A female patient in their mid-80s or older, a dermoscopic close-up of a skin lesion:
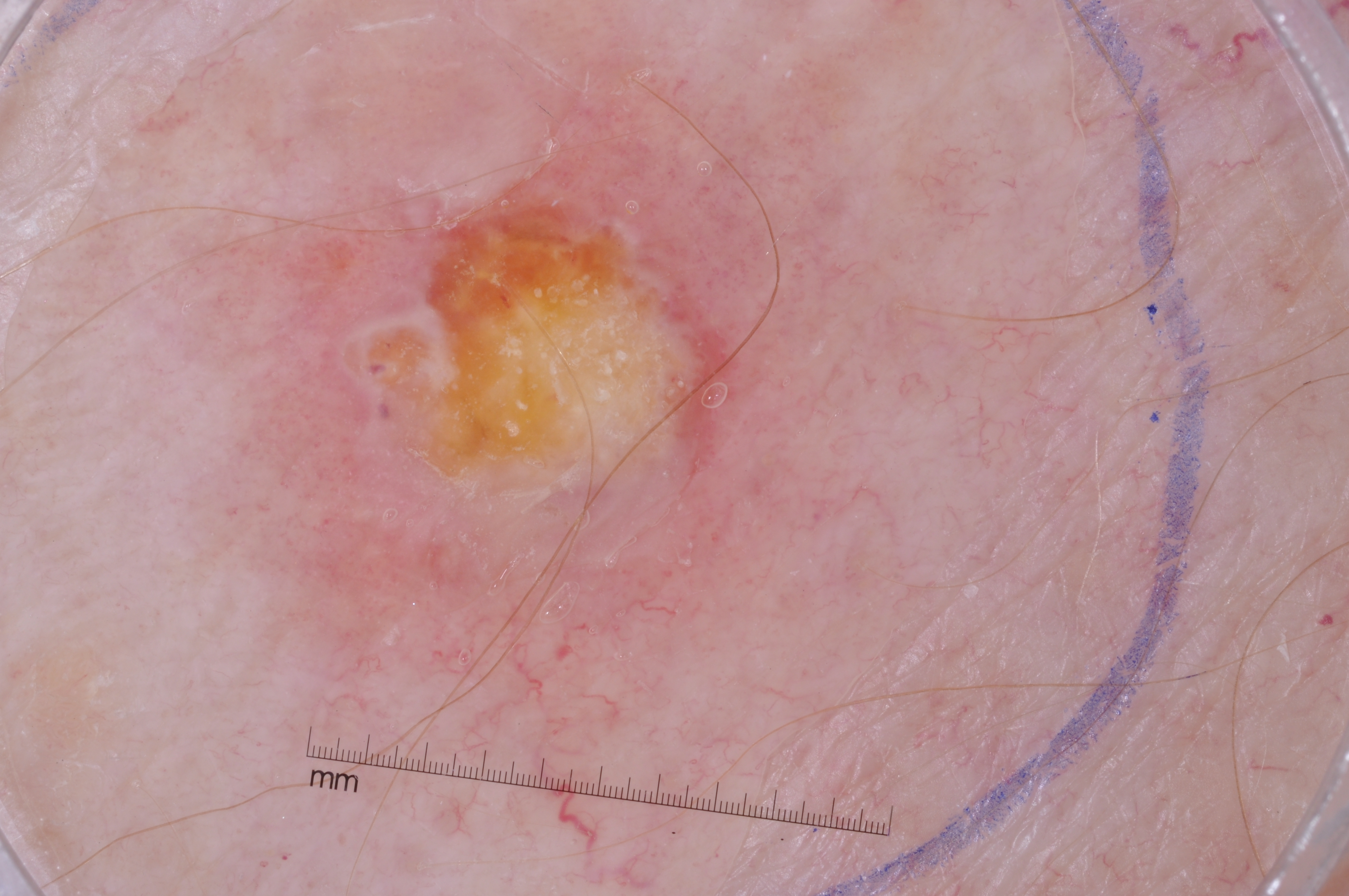extent = ~35% of the field
dermoscopic findings = milia-like cysts; absent: pigment network, negative network, and streaks
lesion bbox = <bbox>127, 10, 854, 743</bbox>
diagnosis = a seborrheic keratosis